A dermoscopic close-up of a skin lesion: 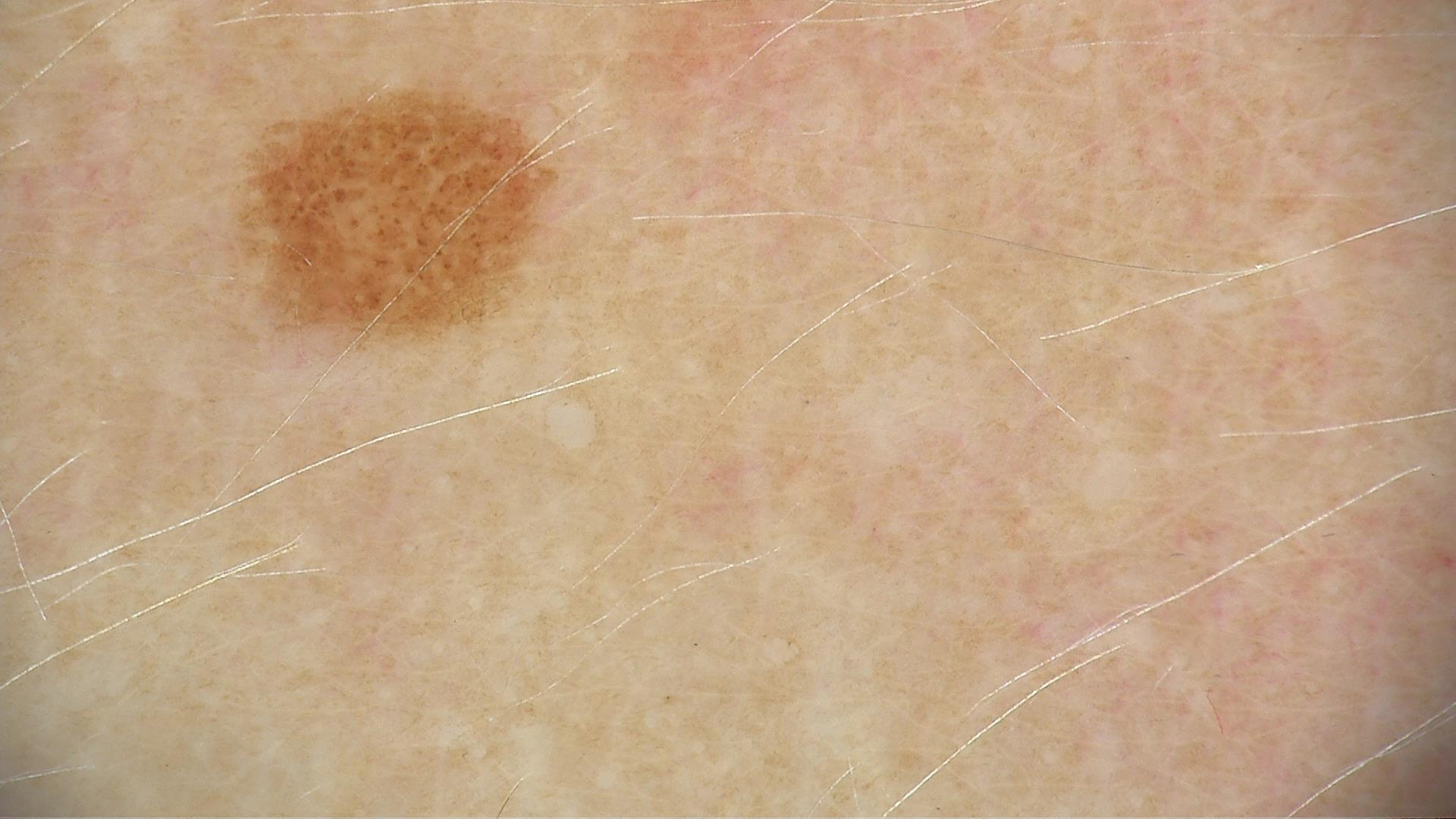Classified as a dysplastic junctional nevus.